This image was taken at an angle — 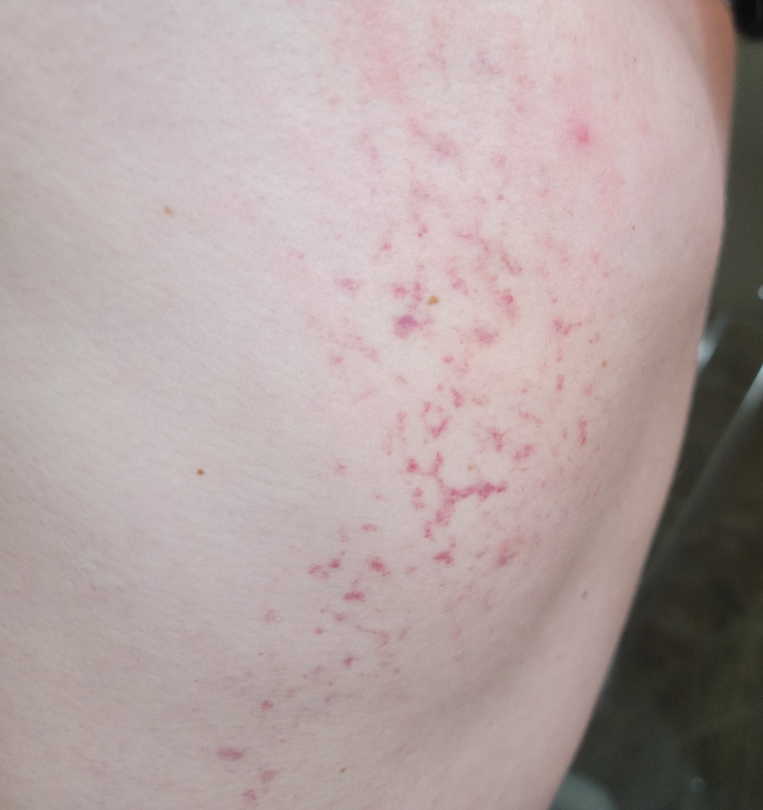Q: Could the case be diagnosed?
A: not assessable
Q: What is the patient's skin tone?
A: FST II
Q: Texture?
A: flat
Q: Reported symptoms?
A: bothersome appearance
Q: Duration?
A: less than one week